This image was taken at an angle; the subject is female; the leg is involved:
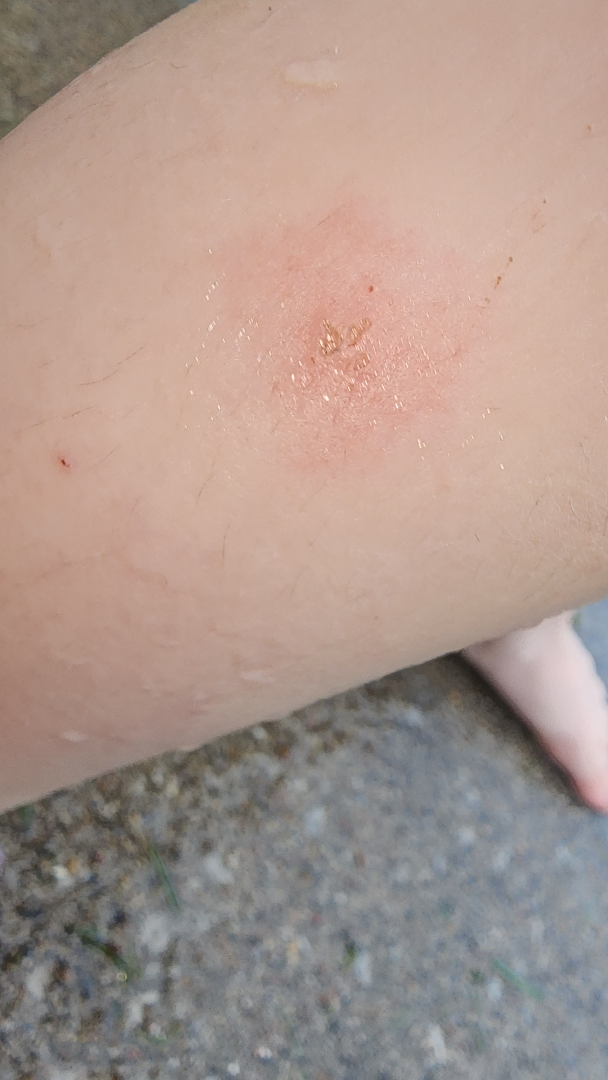Review: Insect Bite (29%); Eczema (23%); Acute dermatitis, NOS (23%); Skin infection (17%); Contact dermatitis, NOS (8%).